The photograph is a close-up of the affected area.
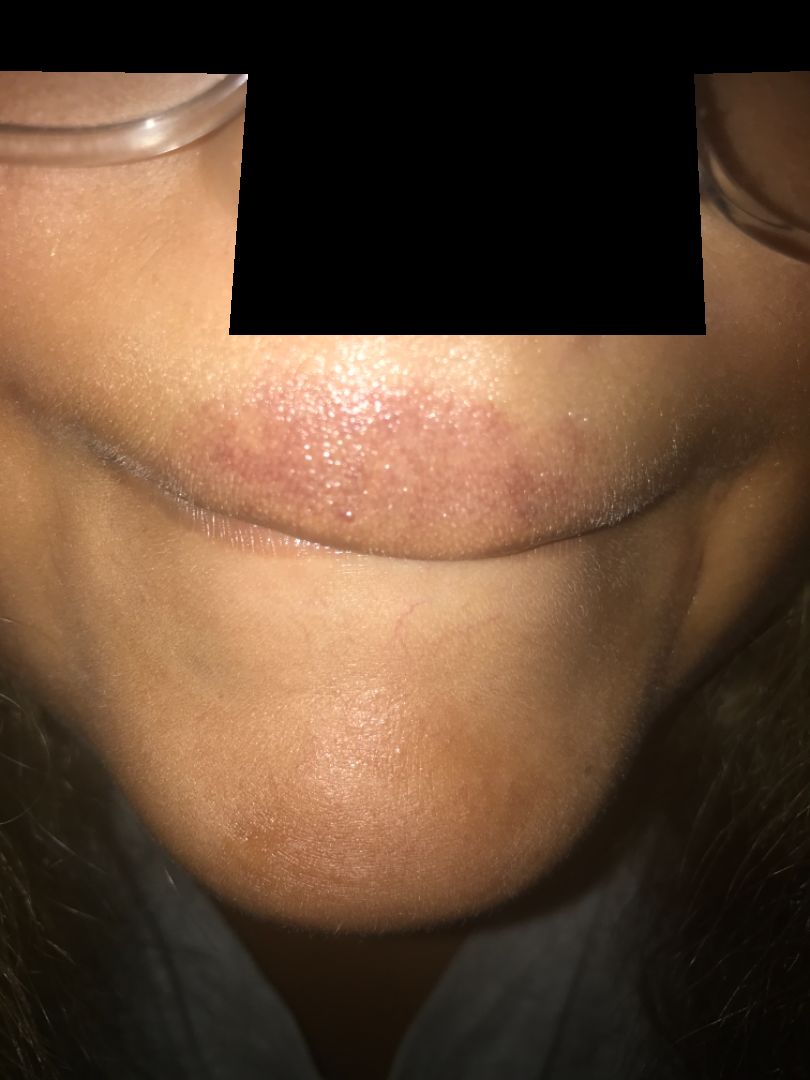Q: What conditions are considered?
A: Irritant Contact Dermatitis (leading); Allergic Contact Dermatitis (considered)